A dermoscopic photograph of a skin lesion.
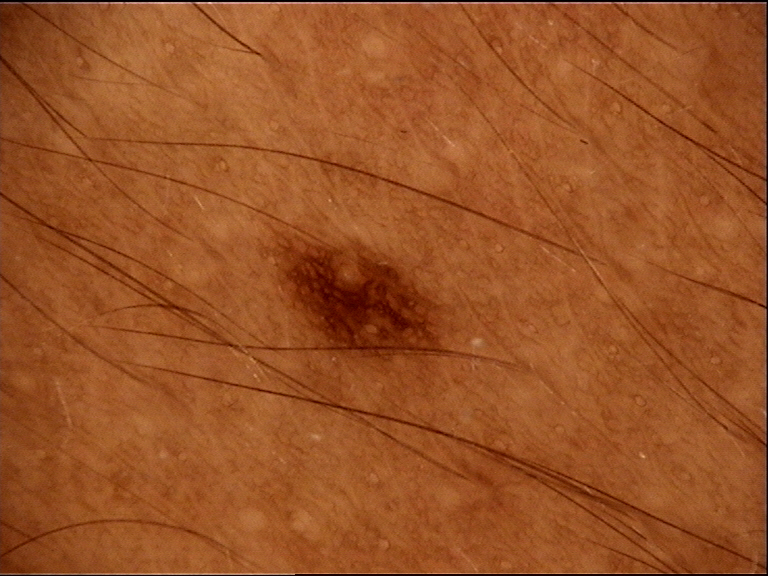Findings:
- assessment — dysplastic junctional nevus (expert consensus)